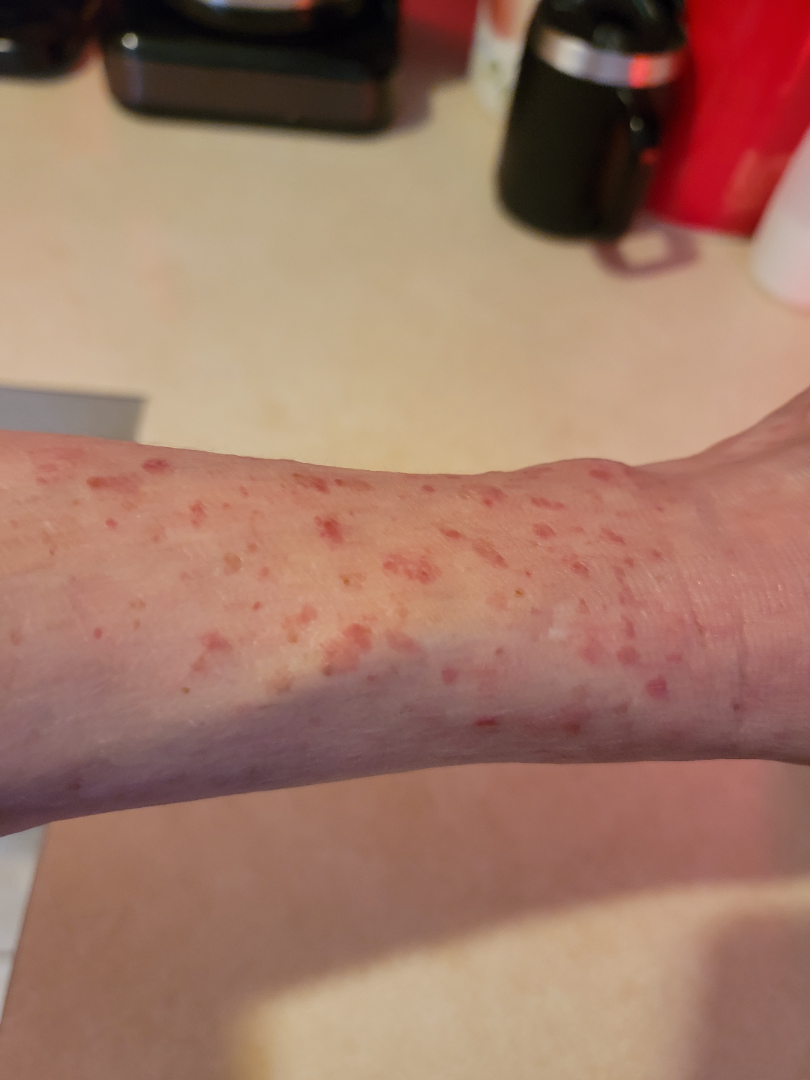The contributor is a female aged 50–59. The photograph is a close-up of the affected area. The affected area is the arm, leg and back of the hand. The reviewing dermatologist's impression was: the differential, in no particular order, includes Viral Exanthem, Lichen planus/lichenoid eruption and Actinic Keratosis.